The subject is 50–59, female. The contributor reports the lesion is raised or bumpy. Reported lesion symptoms include bothersome appearance and enlargement. The patient considered this a rash. Skin tone: Fitzpatrick phototype V; human graders estimated MST 5 or 6. Reported duration is about one day. An image taken at a distance: 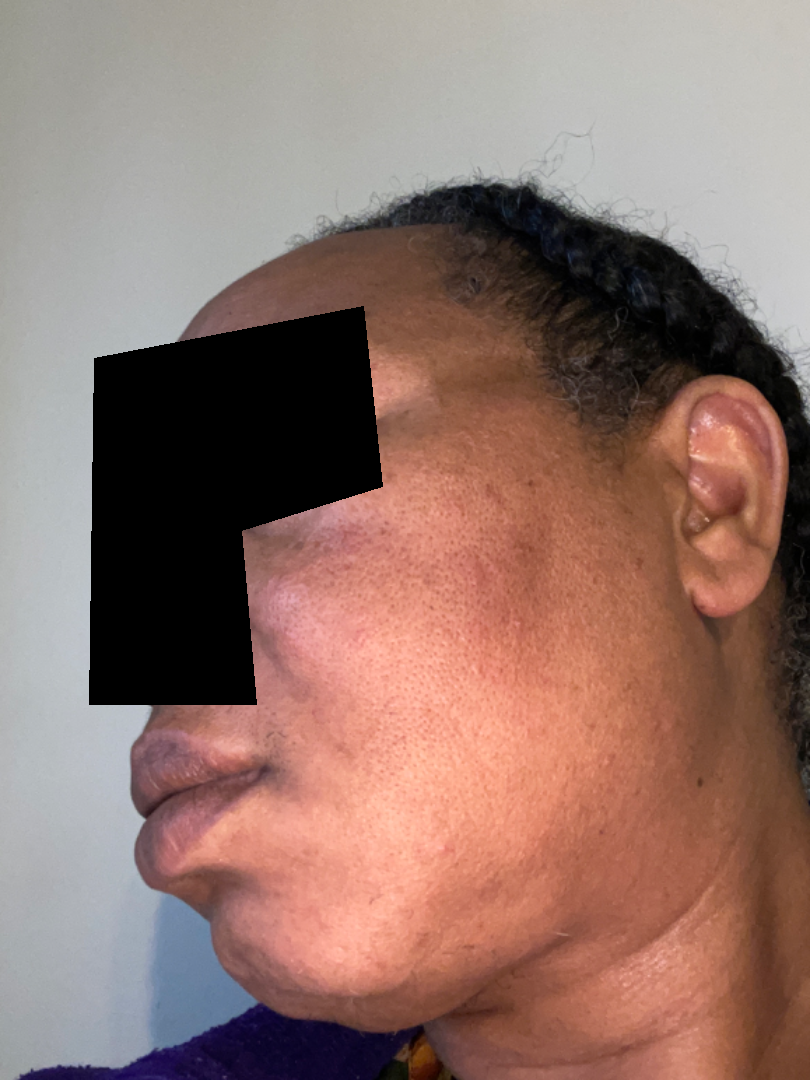On dermatologist assessment of the image, Acne (possible); Rosacea (possible).